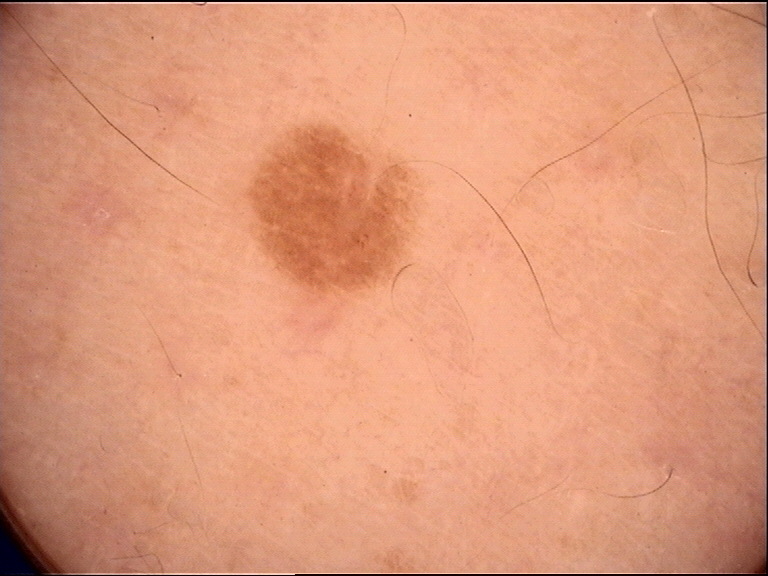modality=dermatoscopy; class=dysplastic junctional nevus (expert consensus).